The photo was captured at an angle. The contributor reports the lesion is raised or bumpy and rough or flaky. Present for three to twelve months. The affected area is the back of the hand. The patient reported no systemic symptoms. Reported lesion symptoms include itching, pain, darkening and bothersome appearance — 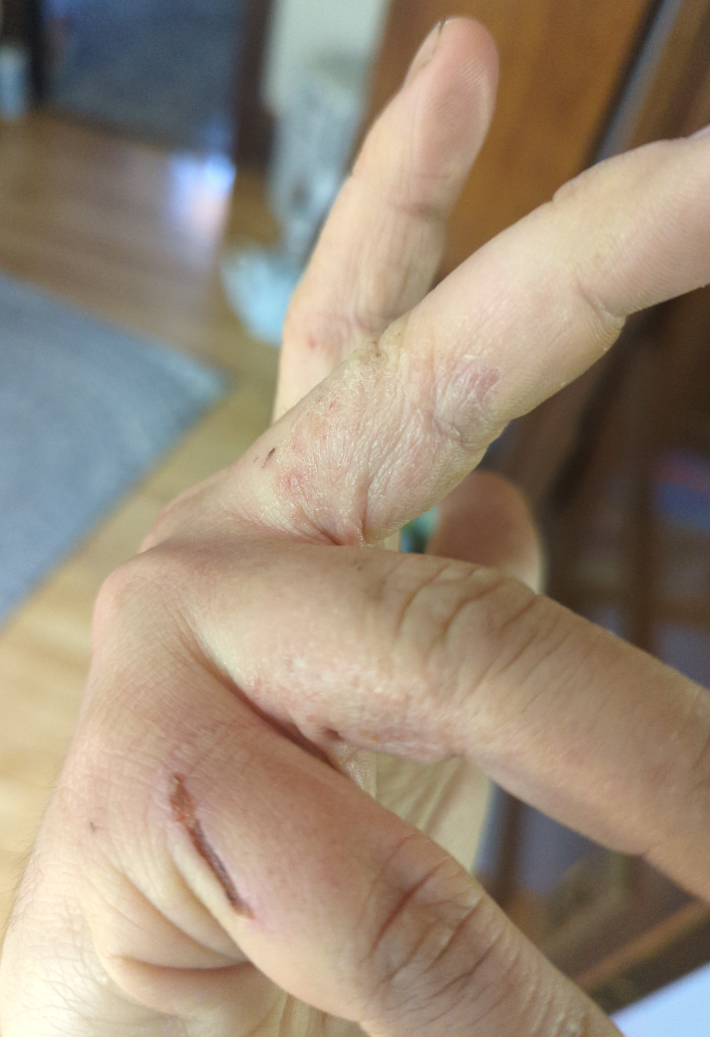Q: What was the assessment?
A: unable to determine